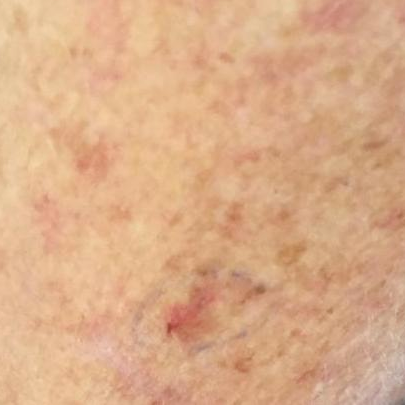{"patient": {"age": 65}, "image": "clinical photograph", "lesion_location": "an arm", "symptoms": {"present": ["itching"]}, "diagnosis": {"name": "actinic keratosis", "code": "ACK", "malignancy": "indeterminate", "confirmation": "clinical consensus"}}